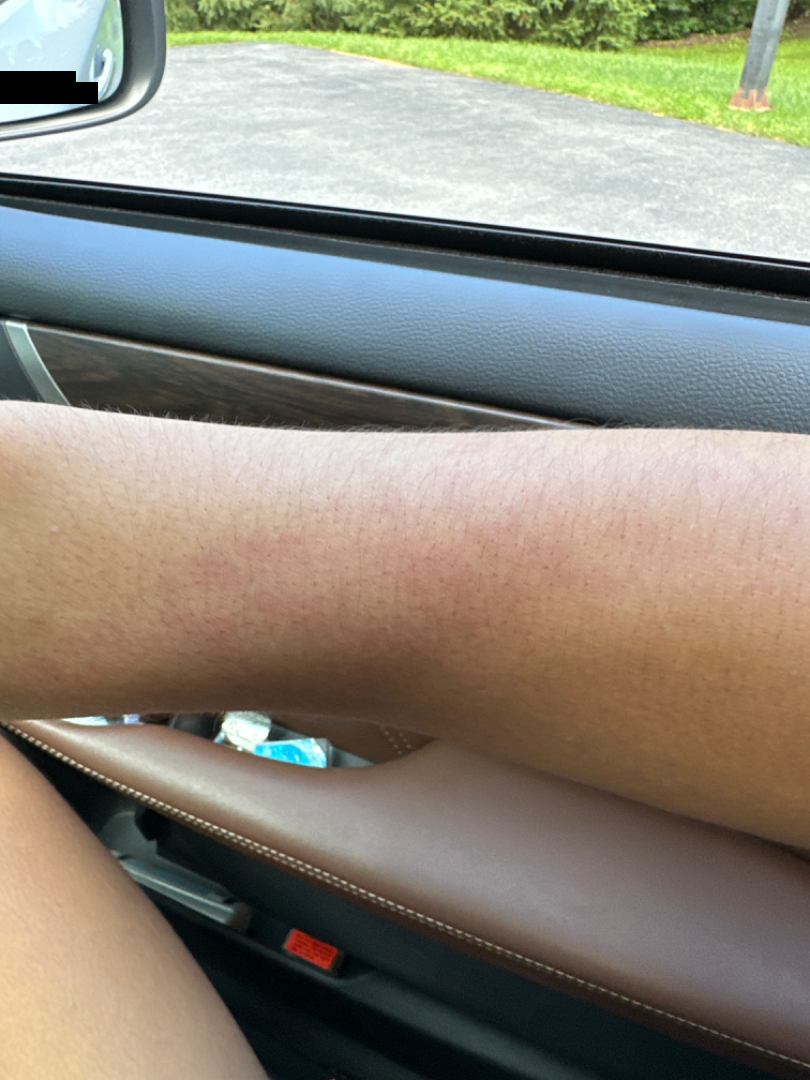The case was difficult to assess from the available photograph.
Located on the arm.
Reported duration is about one day.
Fitzpatrick phototype IV.
A close-up photograph.
The patient considered this a rash.
The patient notes bothersome appearance.
Texture is reported as flat.